The contributor notes the condition has been present for less than one week · this image was taken at a distance · symptoms reported: bothersome appearance and itching · the arm is involved · self-categorized by the patient as a rash · the lesion is described as raised or bumpy · male contributor, age 50–59.
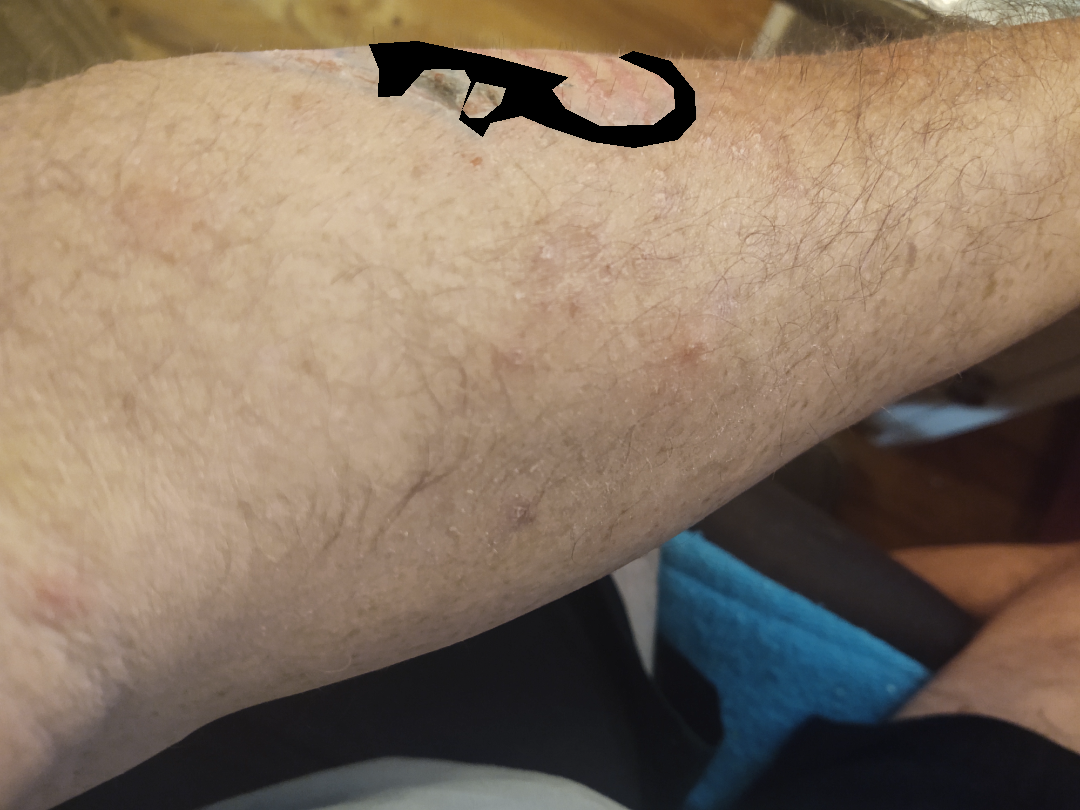clinical impression: Folliculitis (0.67); Irritant Contact Dermatitis (0.33).